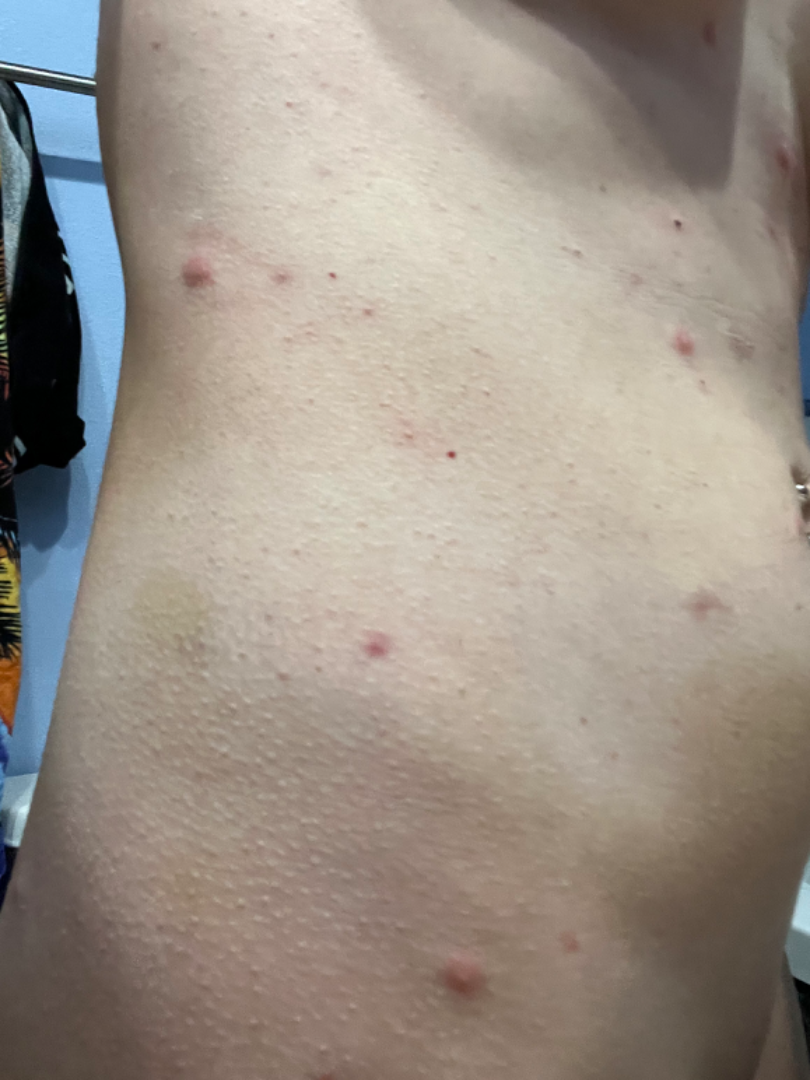Case summary:
• patient-reported symptoms — pain and itching
• anatomic site — front of the torso
• subject — female, age 30–39
• image framing — at an angle
• differential diagnosis — most consistent with Insect Bite; also consider Folliculitis; also raised was Lymphomatoid papulosis